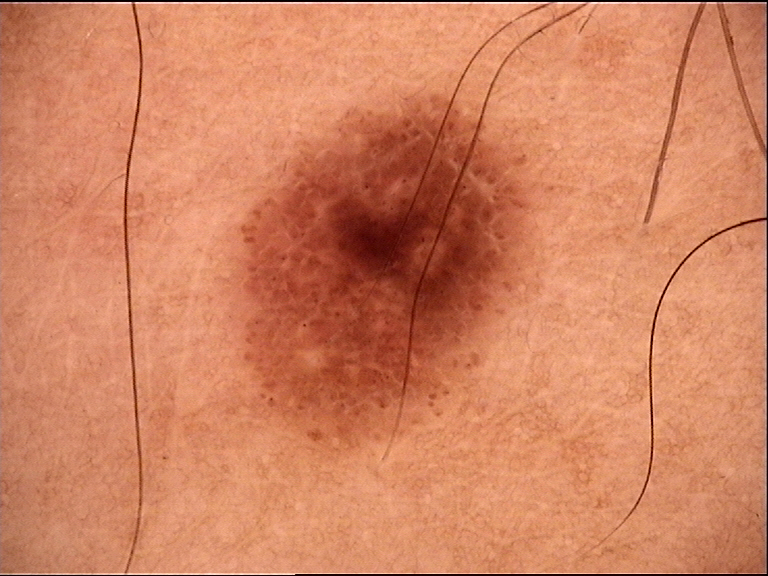The diagnosis was a junctional nevus.